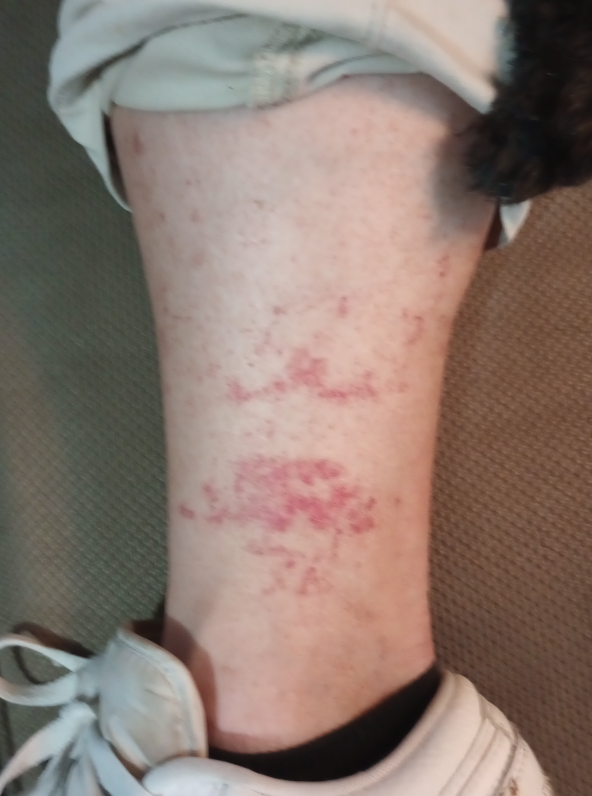shot type=close-up | affected area=leg | subject=female | clinical impression=most likely Pigmented purpuric eruption; a more distant consideration is Contact dermatitis; less probable is Stasis Dermatitis.